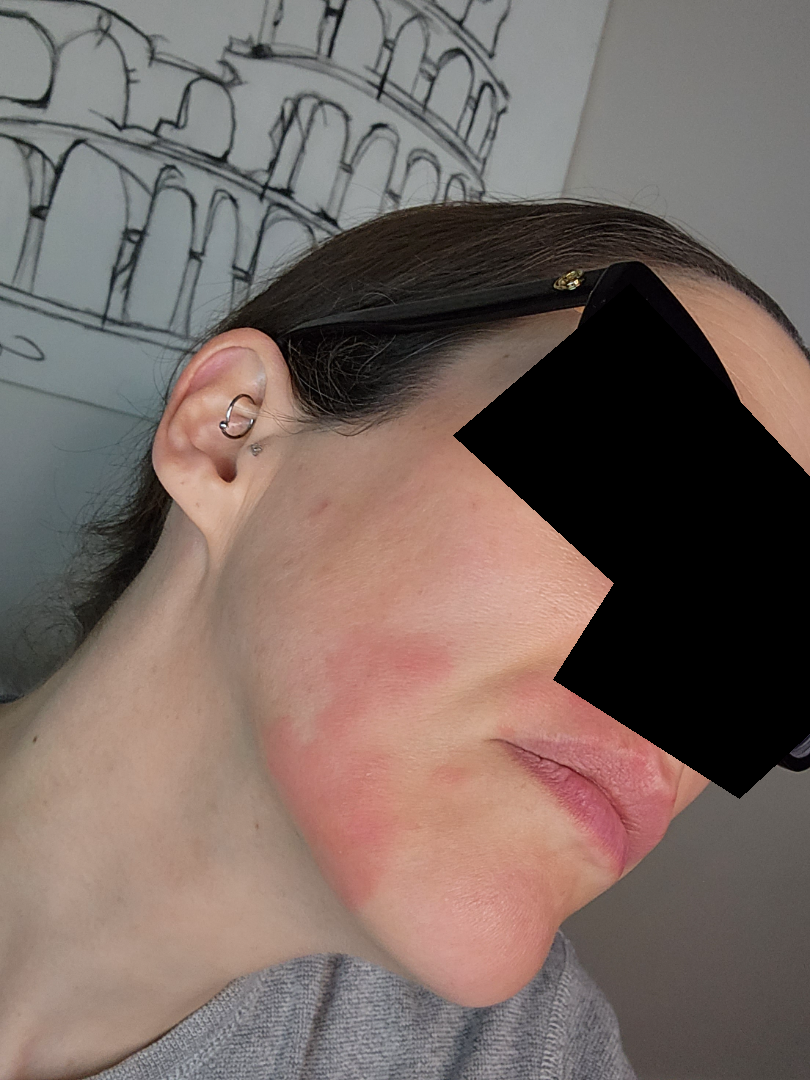The skin findings could not be characterized from the image.
The subject is a female aged 40–49.
The head or neck is involved.
A close-up photograph.